A skin lesion imaged with a dermatoscope.
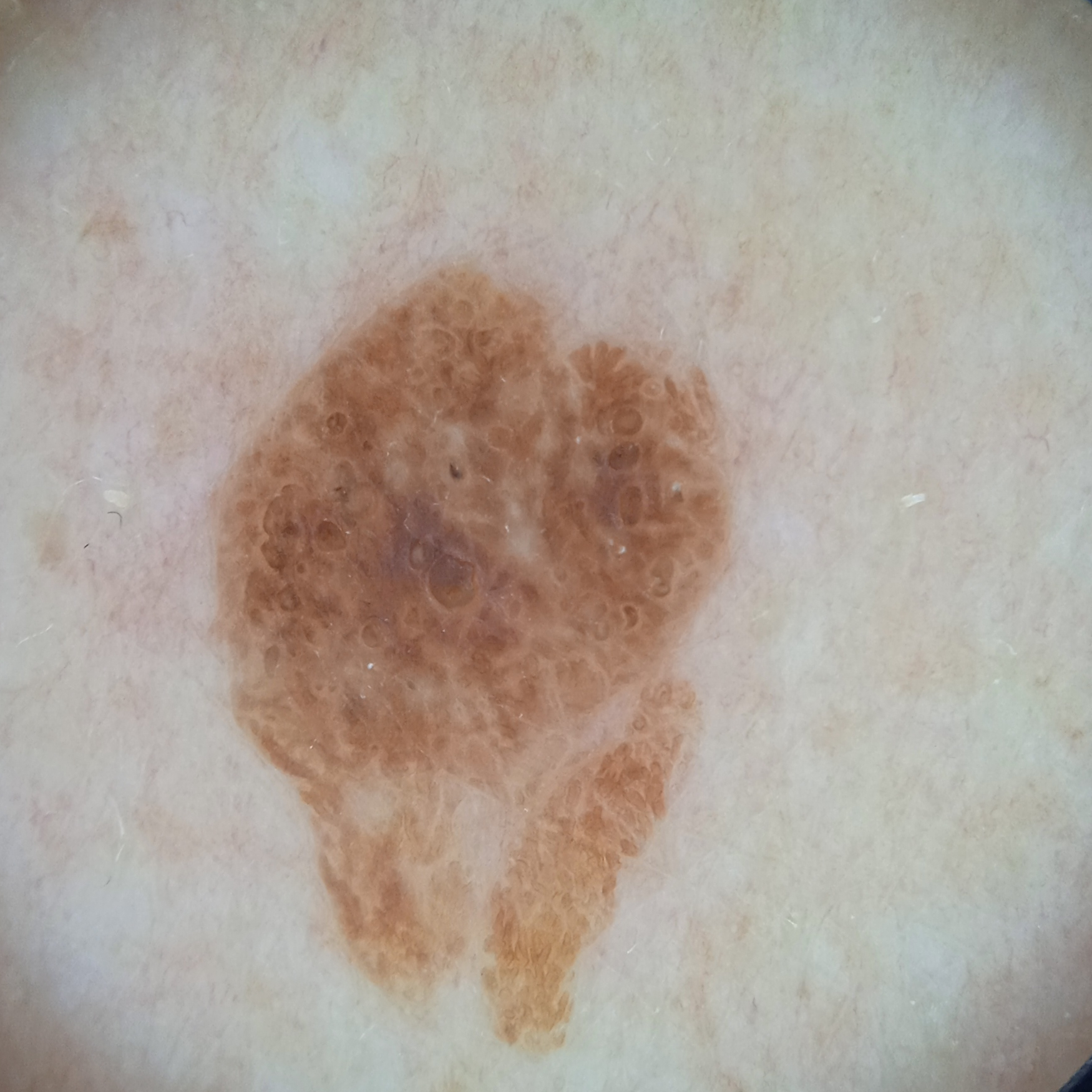lesion_location: the back
lesion_size:
  diameter_mm: 9.6
diagnosis:
  name: seborrheic keratosis
  malignancy: benign